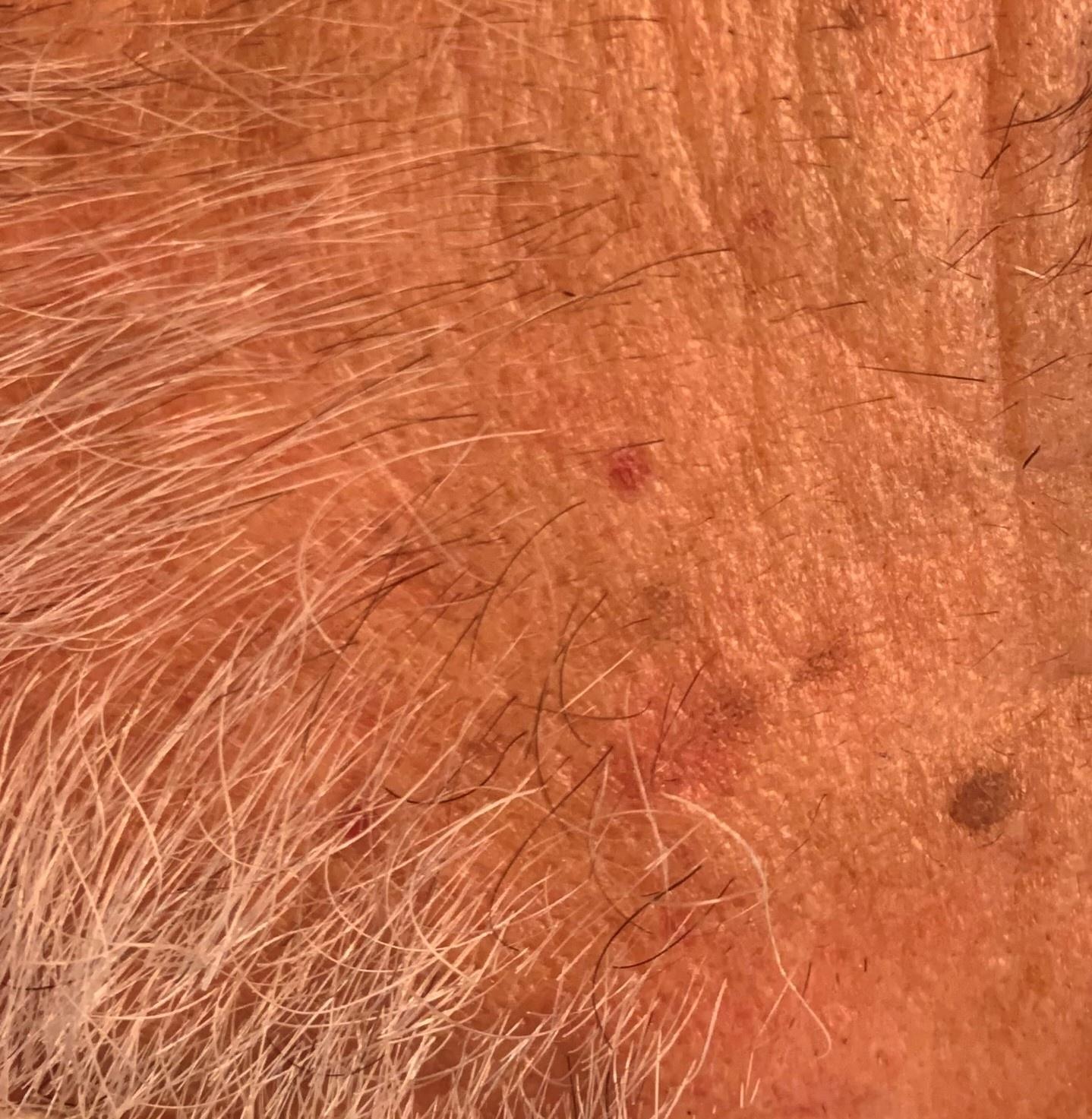The clinical impression was a solar or actinic keratosis.